The contributor reports the condition has been present for one to four weeks. The affected area is the arm, front of the torso and back of the torso. Close-up view. Symptoms reported: itching and bothersome appearance. The contributor reports the lesion is raised or bumpy and rough or flaky. No constitutional symptoms were reported. Self-categorized by the patient as a rash: 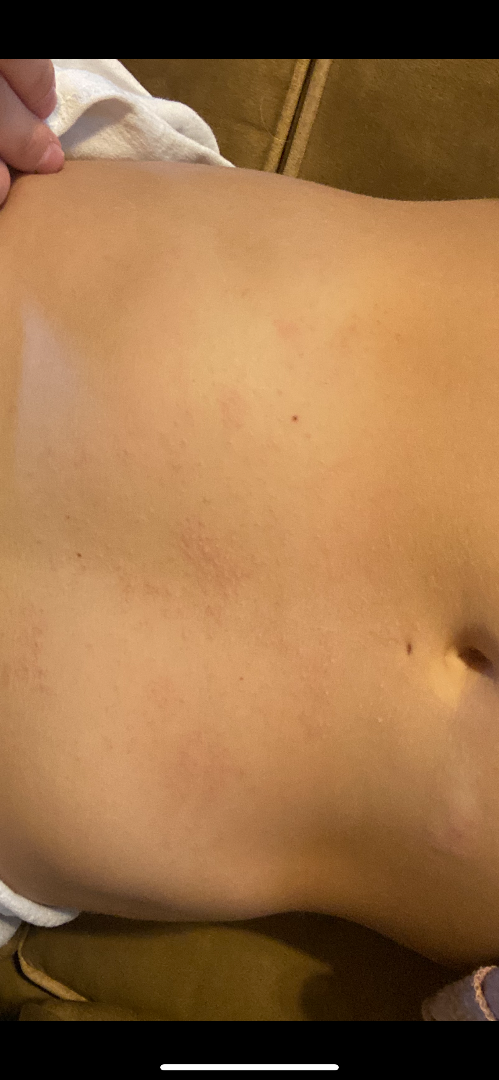<summary>
<assessment>indeterminate from the photograph</assessment>
</summary>